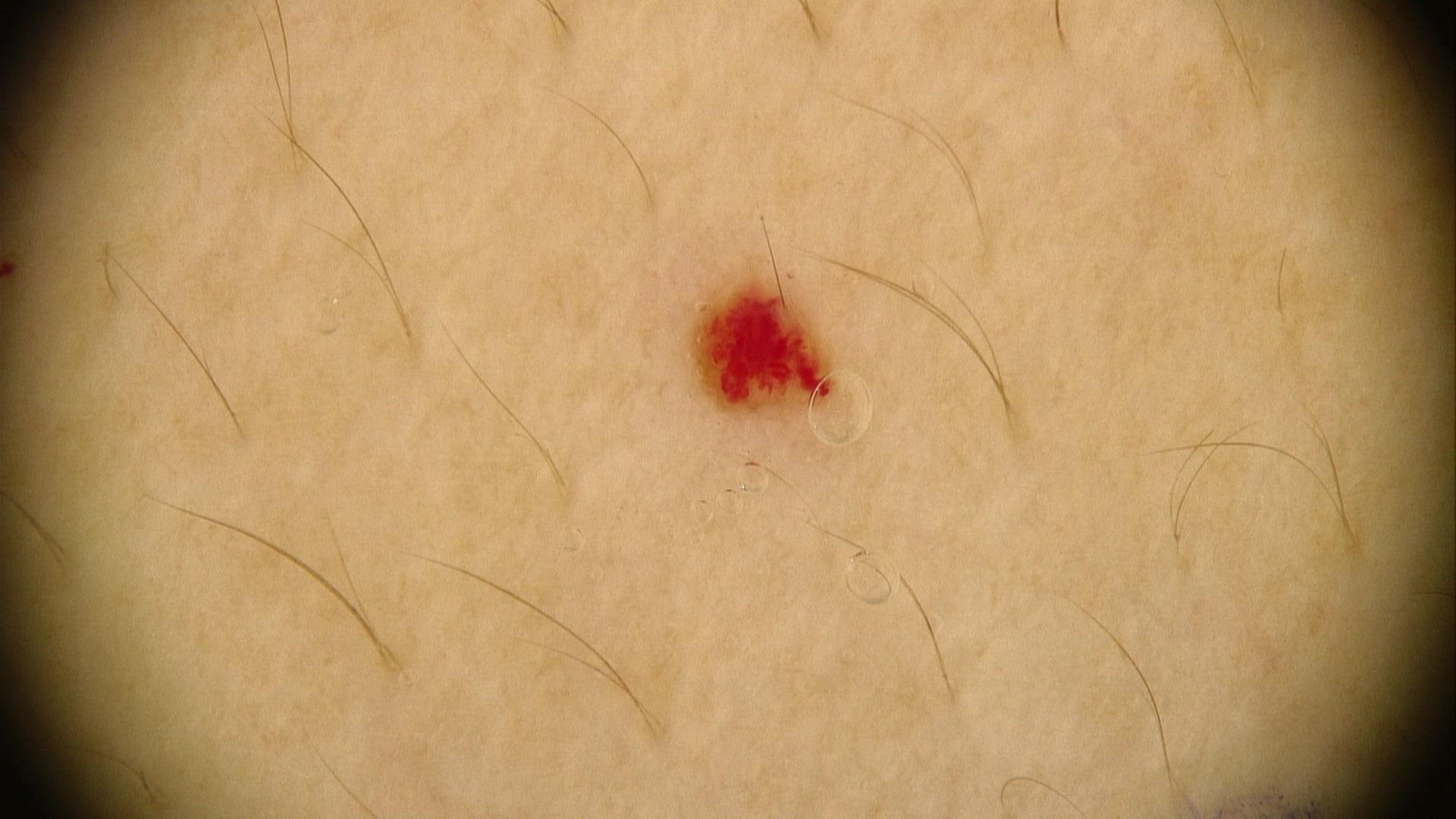Notes:
– assessment — vascular lesion